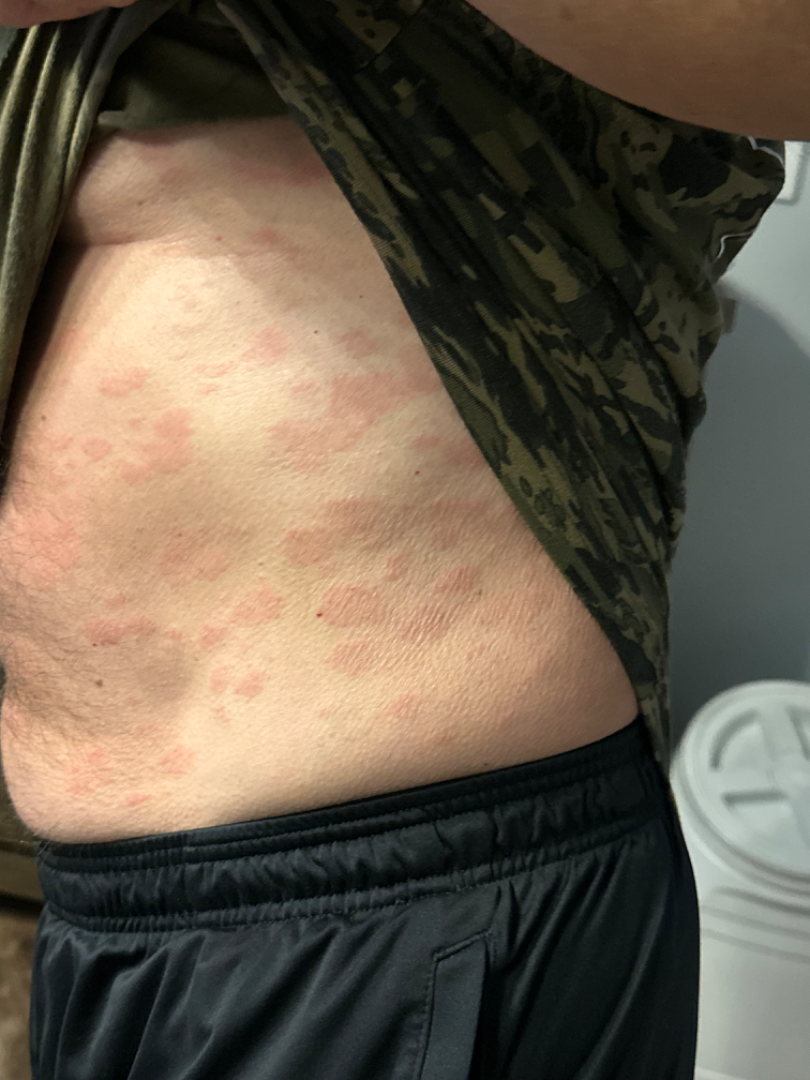History: Located on the front of the torso. A close-up photograph. The patient is male. Impression: Drug Rash, Pityriasis rosea and Syphilis were each considered, in no particular order.